The patient notes the condition has been present for less than one week; located on the arm and leg; the patient considered this a rash; symptoms reported: enlargement, itching, burning and bothersome appearance; the subject is a female aged 40–49; the lesion is described as raised or bumpy; skin tone: FST IV; a close-up photograph — 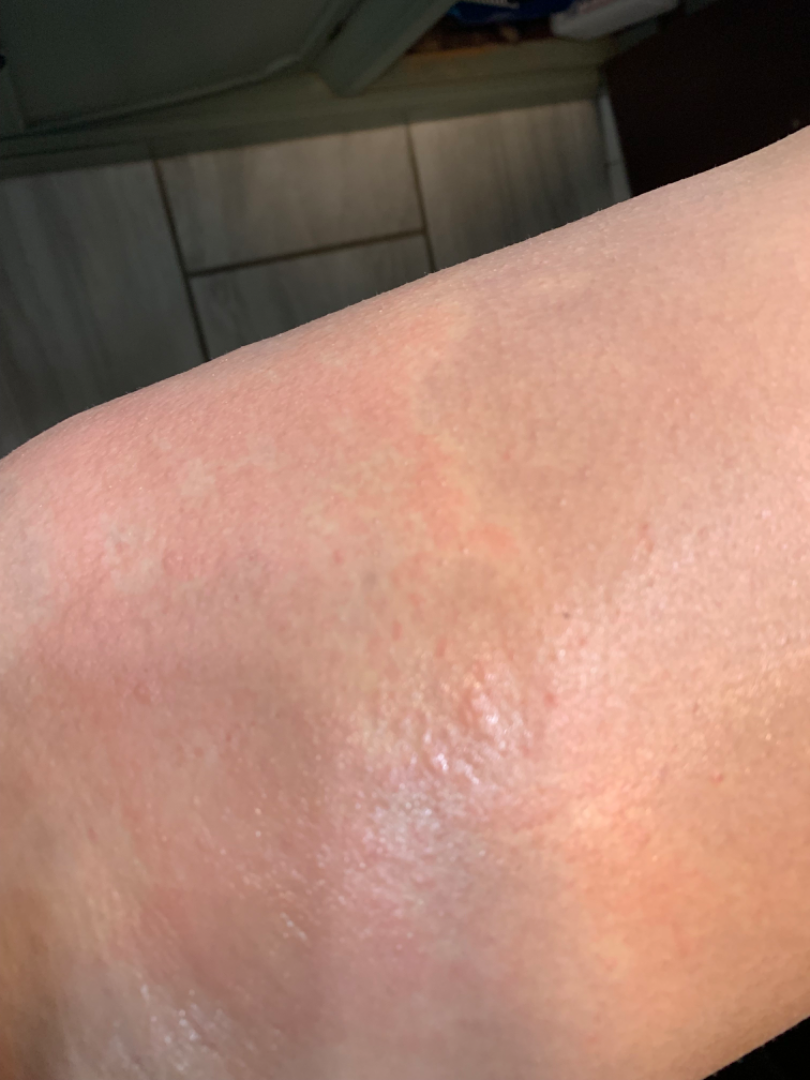Reviewed remotely by one dermatologist: the impression on review was Urticaria.